The contributor is a female aged 40–49. The lesion involves the leg. The photograph was taken at a distance: 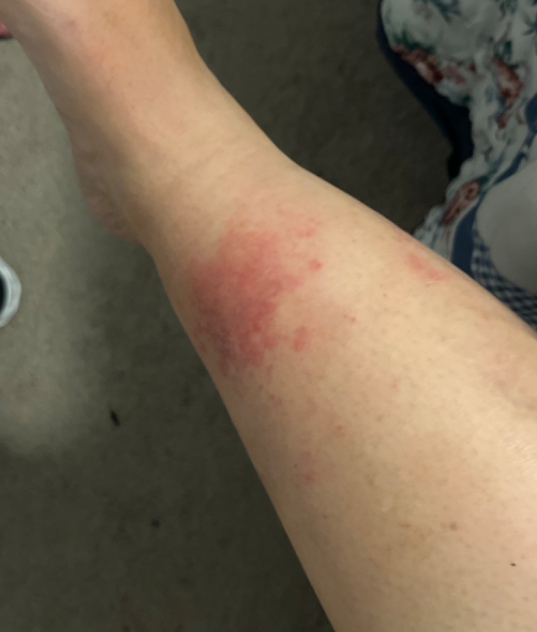<report>
<patient_category>a rash</patient_category>
<duration>about one day</duration>
<skin_tone>
  <monk_skin_tone>3, 5</monk_skin_tone>
</skin_tone>
<symptoms>none reported</symptoms>
<differential>
  <leading>Stasis Dermatitis</leading>
</differential>
</report>